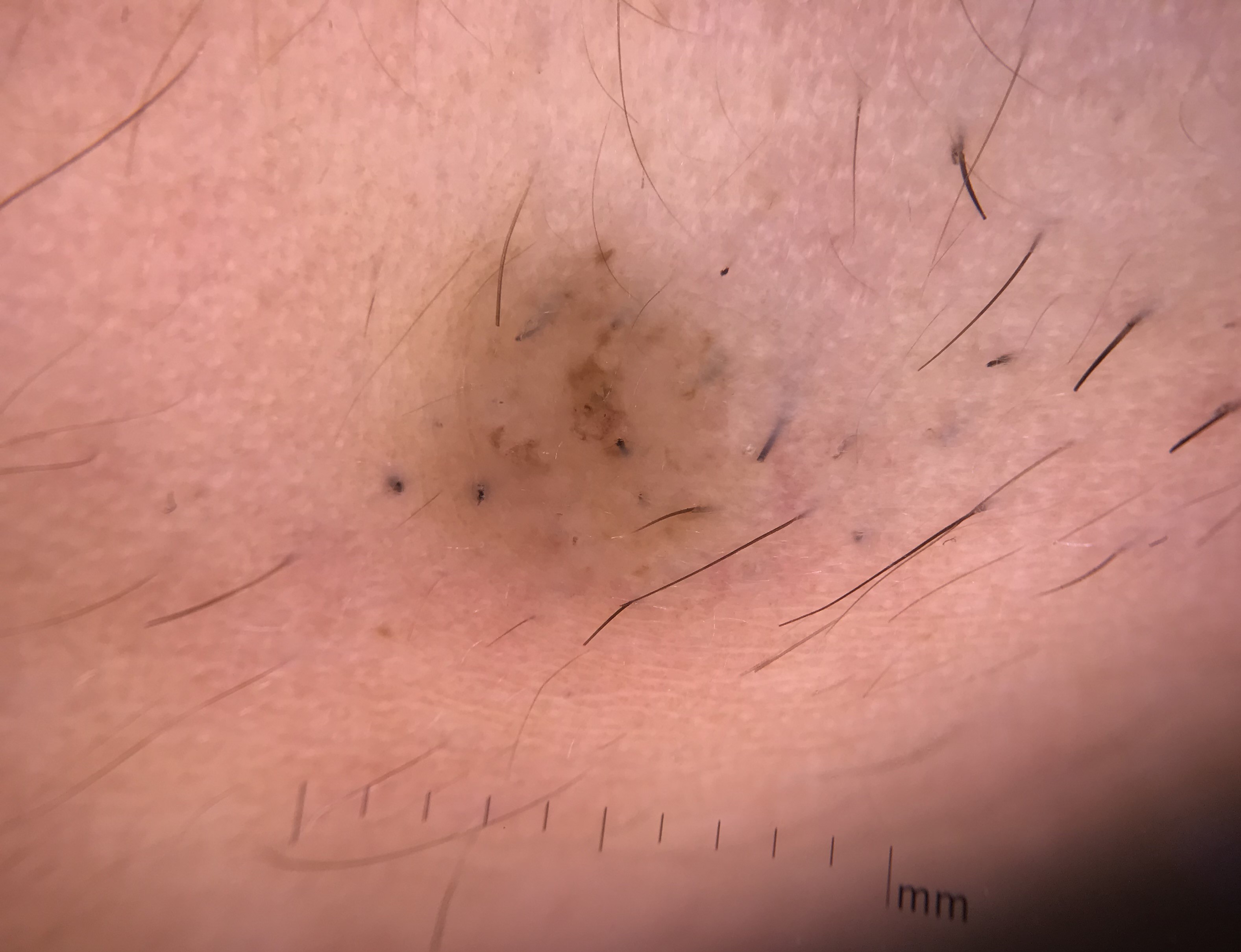Consistent with a banal lesion — a Miescher nevus.